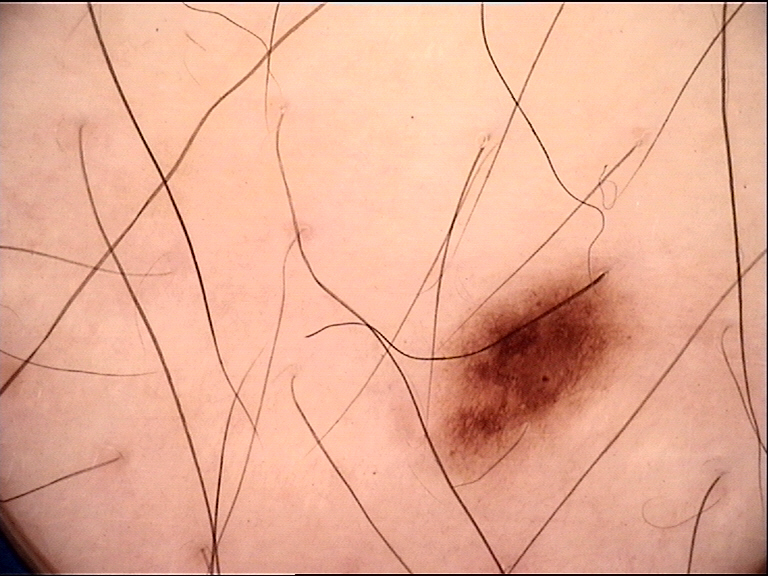label = dysplastic junctional nevus (expert consensus).